Present for one to four weeks. The lesion is described as raised or bumpy and flat. A close-up photograph. Symptoms reported: itching. Self-categorized by the patient as a rash — 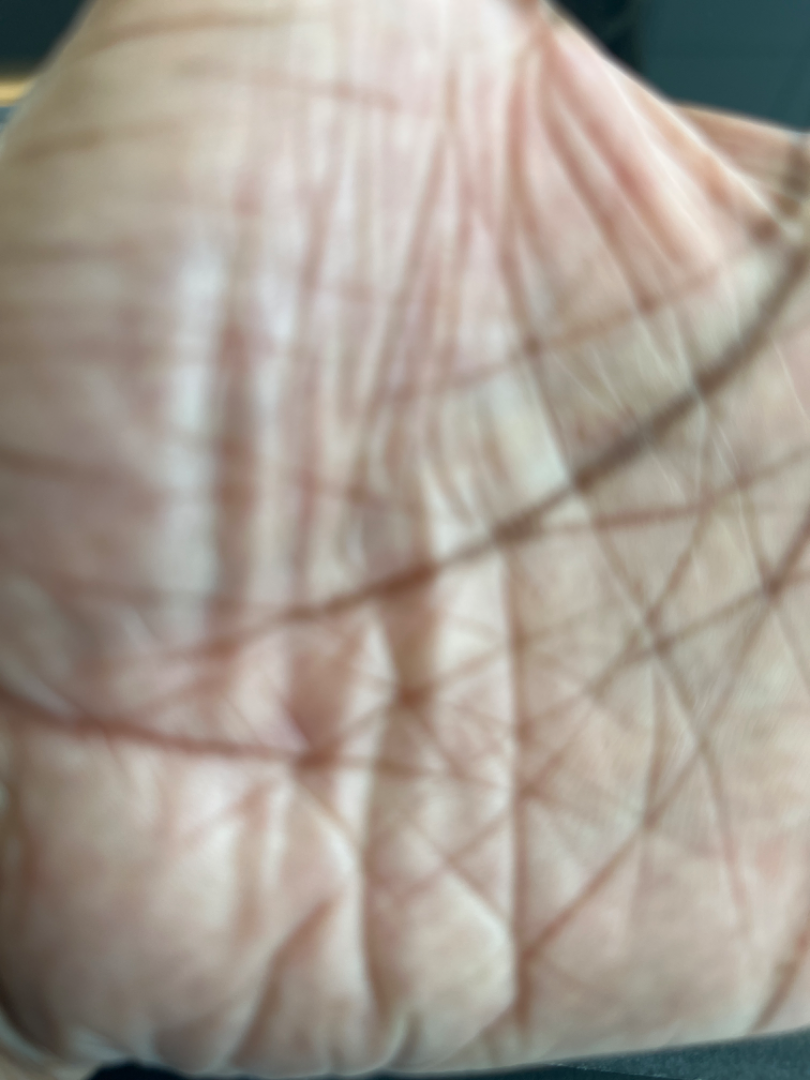On teledermatology review, in keeping with Eczema.